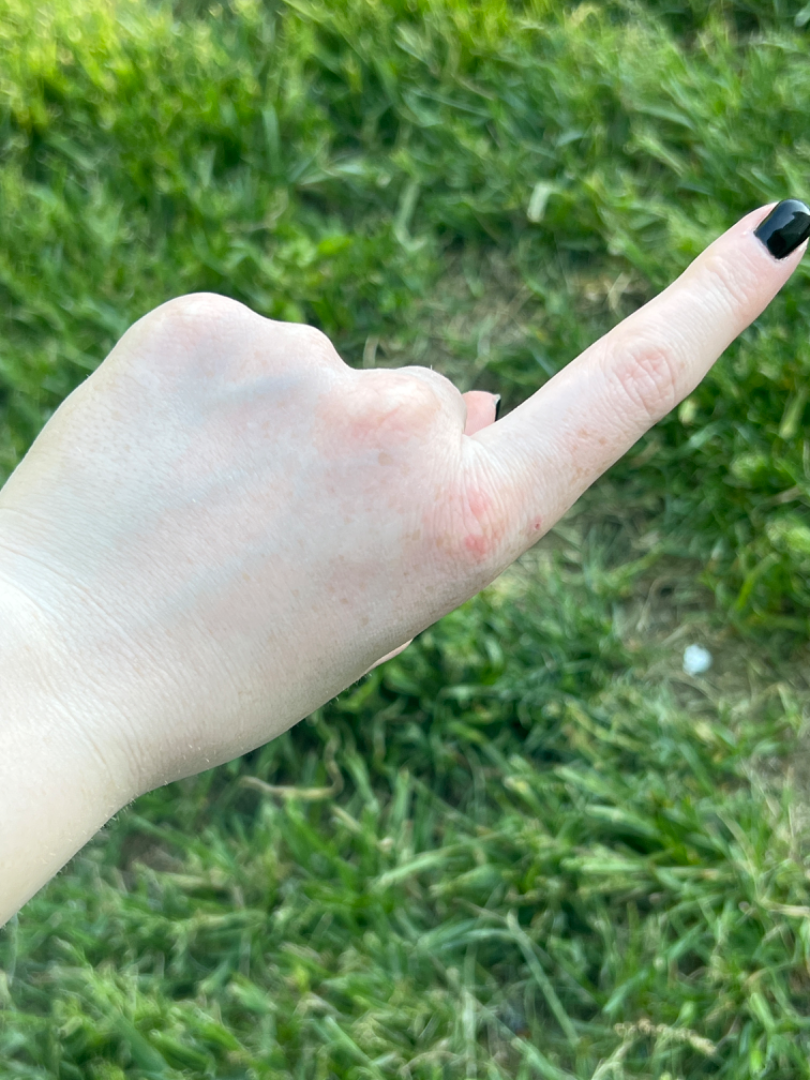<dermatology_case>
<differential>
  <leading>Allergic Contact Dermatitis</leading>
  <considered>Insect Bite</considered>
  <unlikely>Acute dermatitis, NOS; Folliculitis; Eczema</unlikely>
</differential>
</dermatology_case>